This is a close-up image.
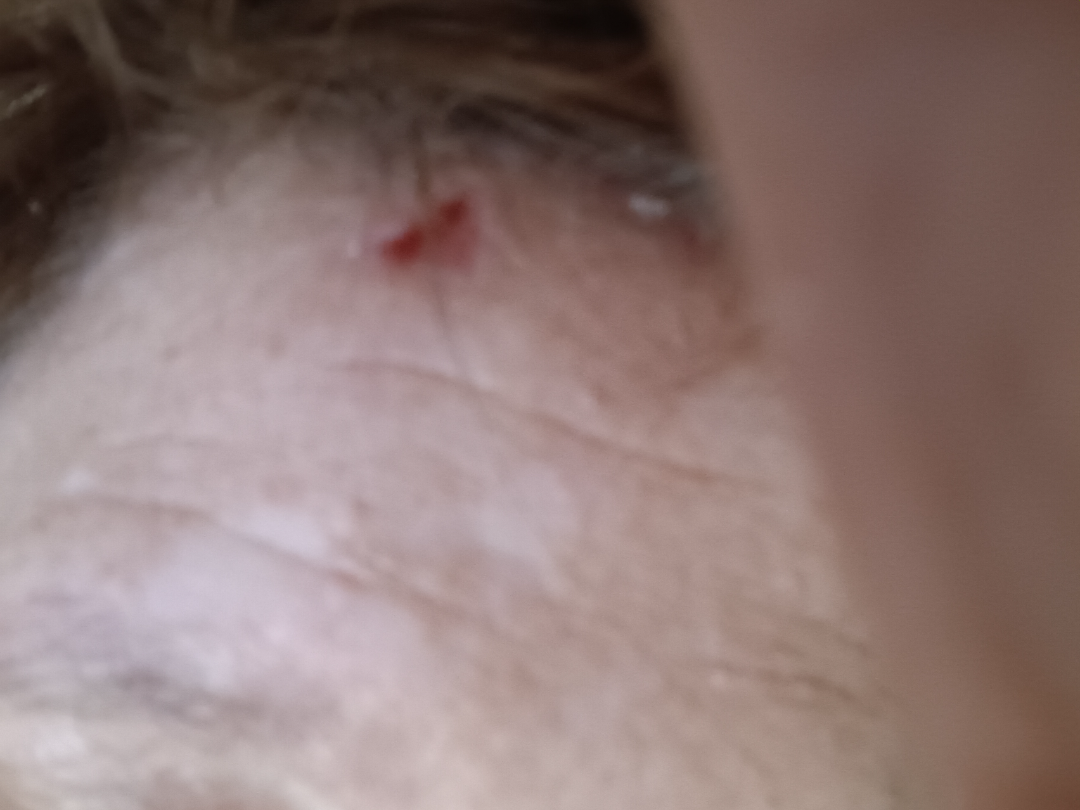Q: What was the assessment?
A: not assessable